The arm is involved; a close-up photograph — 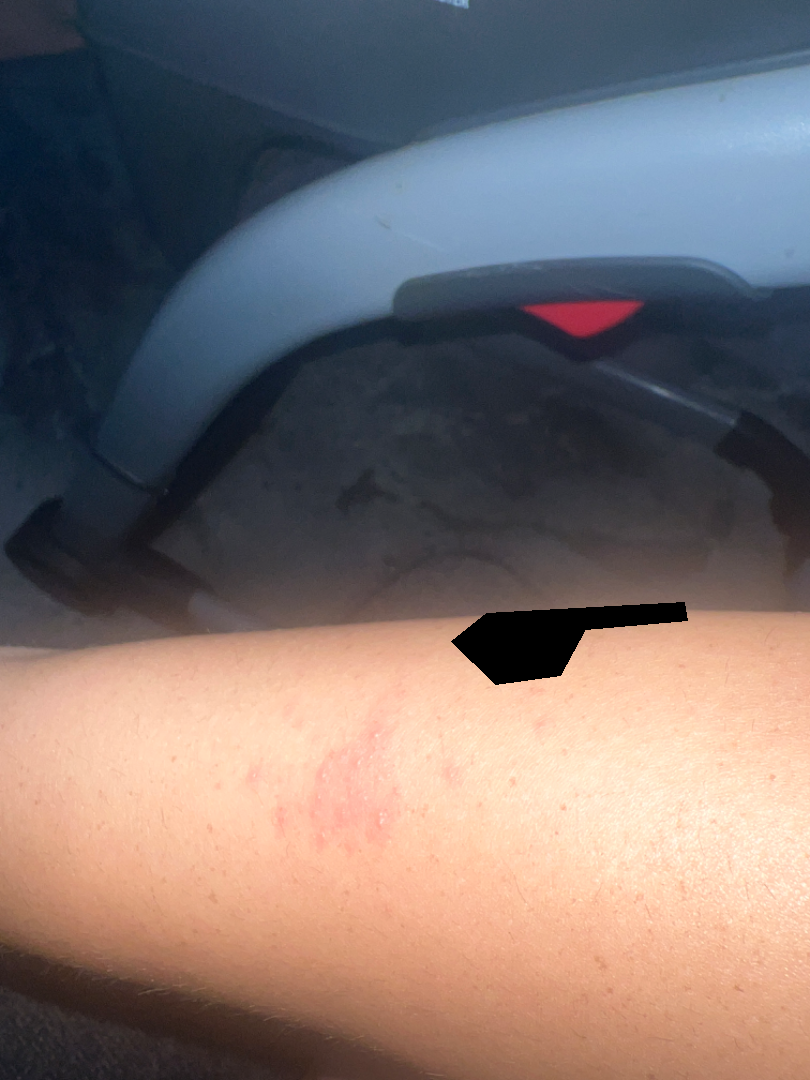Impression: The skin findings could not be characterized from the image.